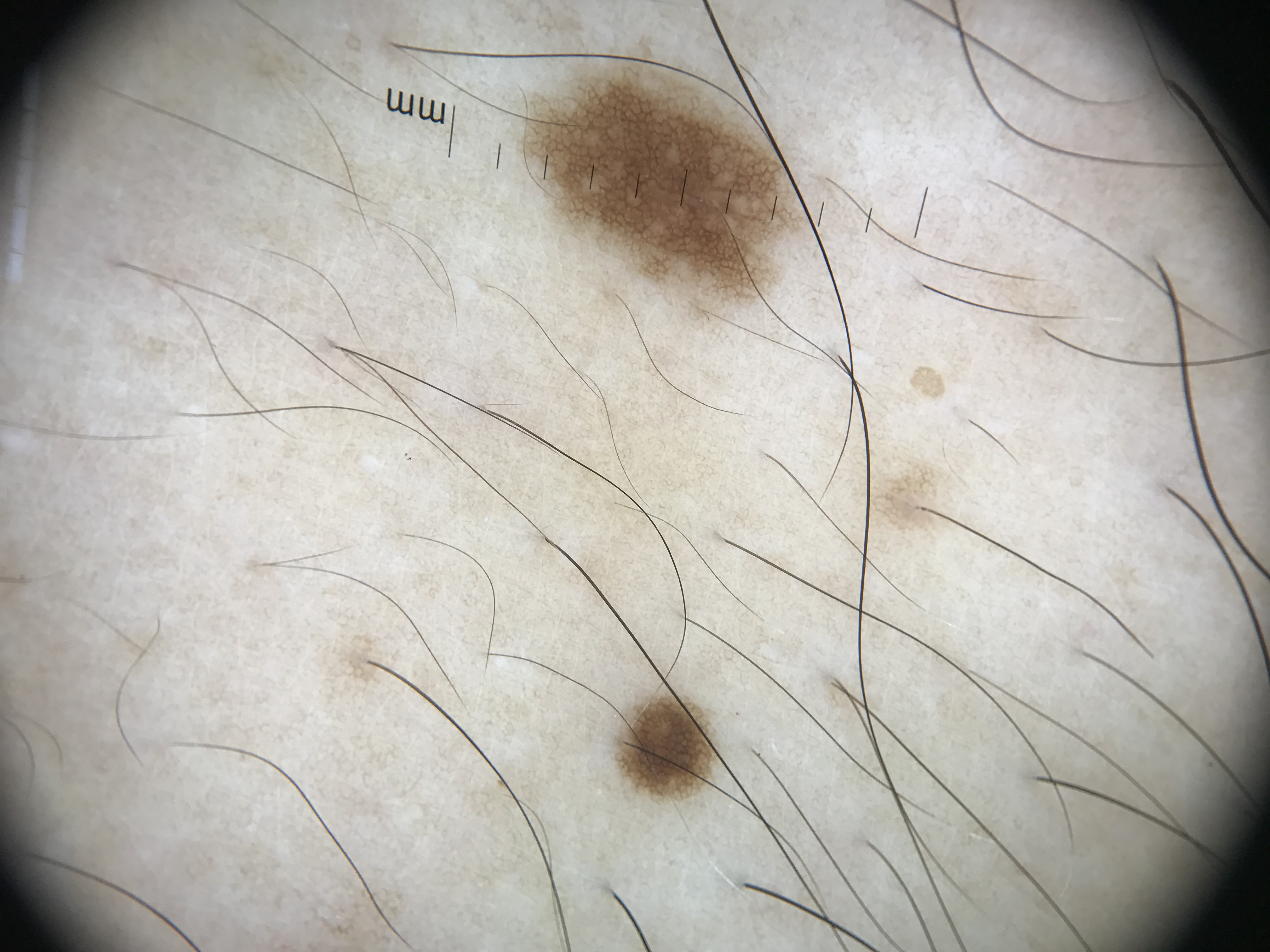The diagnostic label was a junctional nevus.